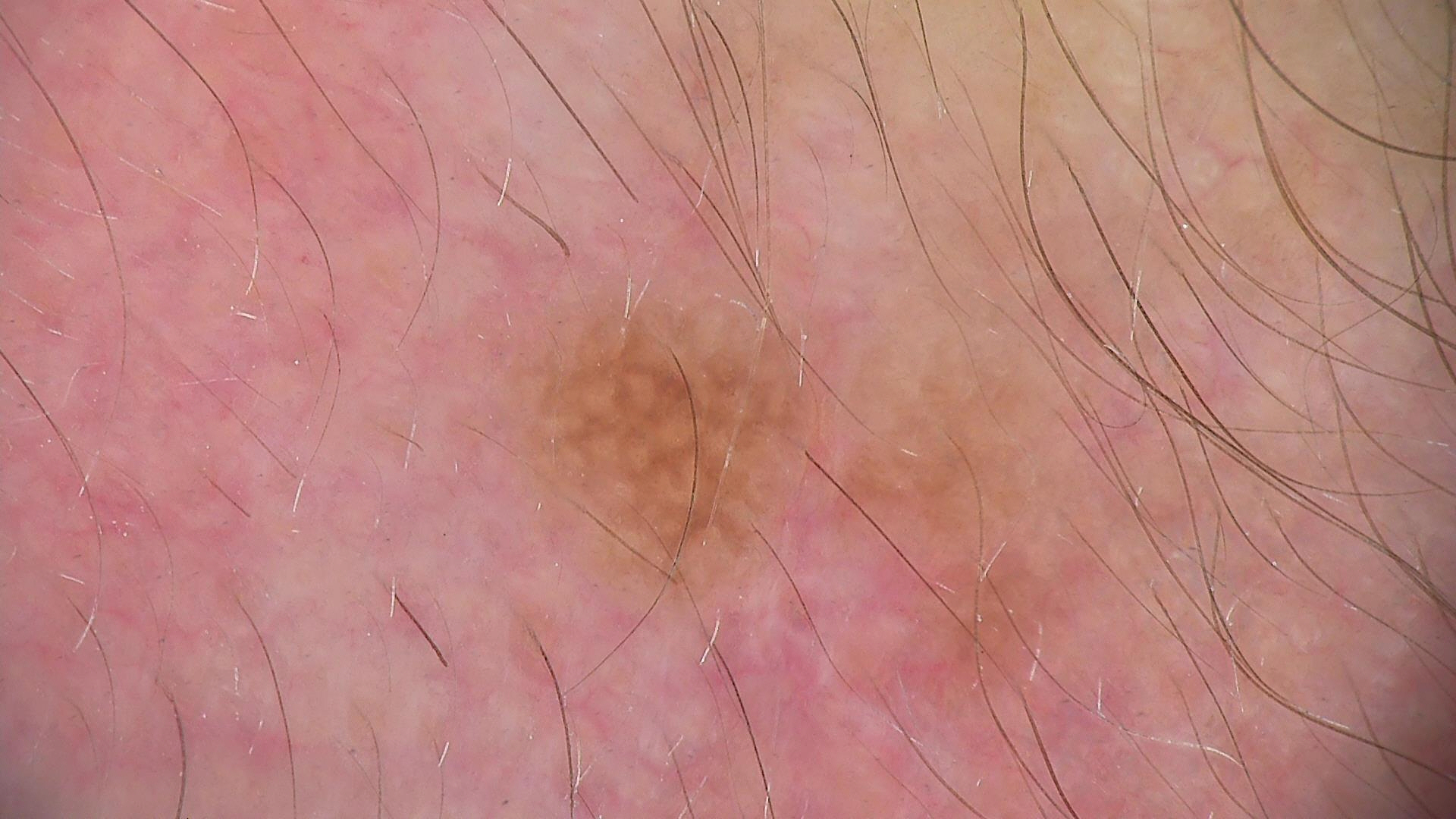image type: dermoscopy
diagnostic label: dysplastic junctional nevus (expert consensus)